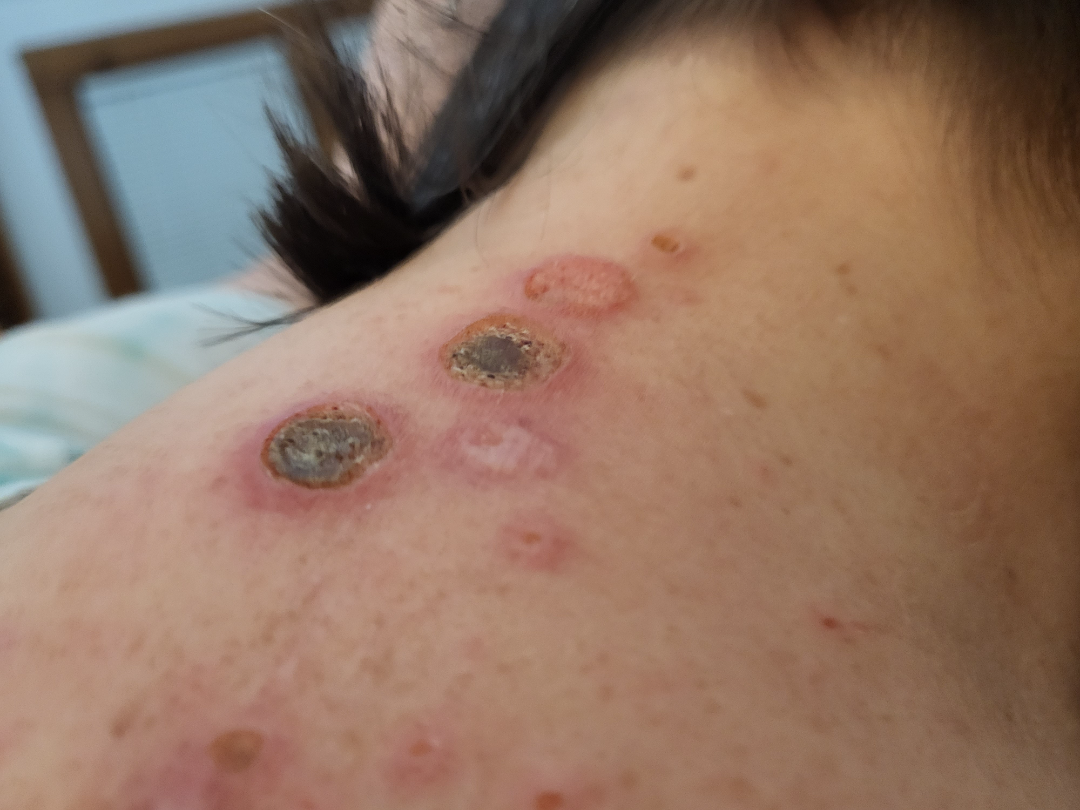| key | value |
|---|---|
| affected area | head or neck |
| patient | female, age 50–59 |
| framing | close-up |
| lesion symptoms | itching and pain |
| surface texture | rough or flaky and raised or bumpy |
| assessment | the favored diagnosis is Ecthyma gangrenosum; also on the differential is Cutaneous polyarteritis nodosa; a remote consideration is Skin lesion in drug addict |